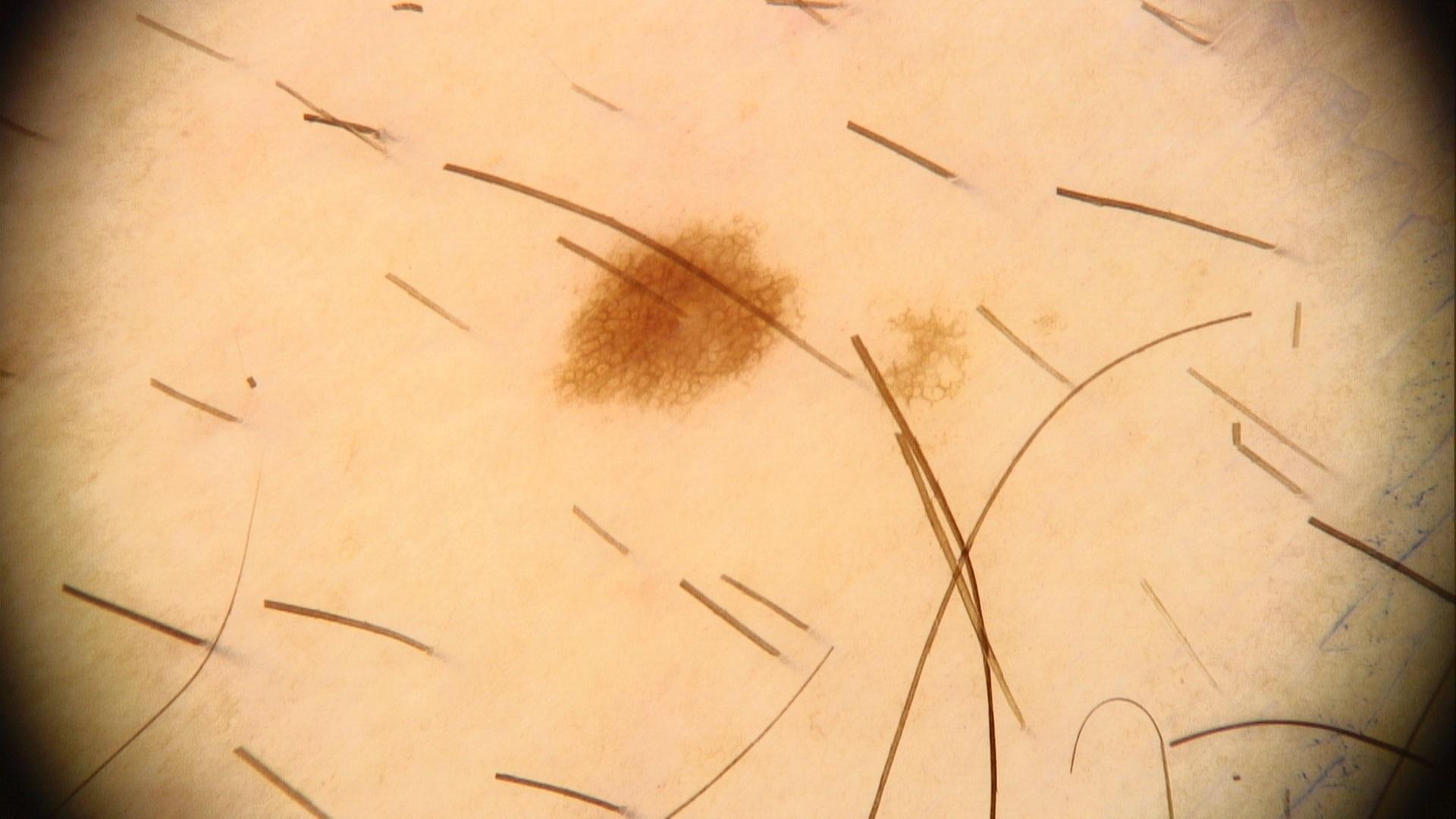Consistent with a nevus.